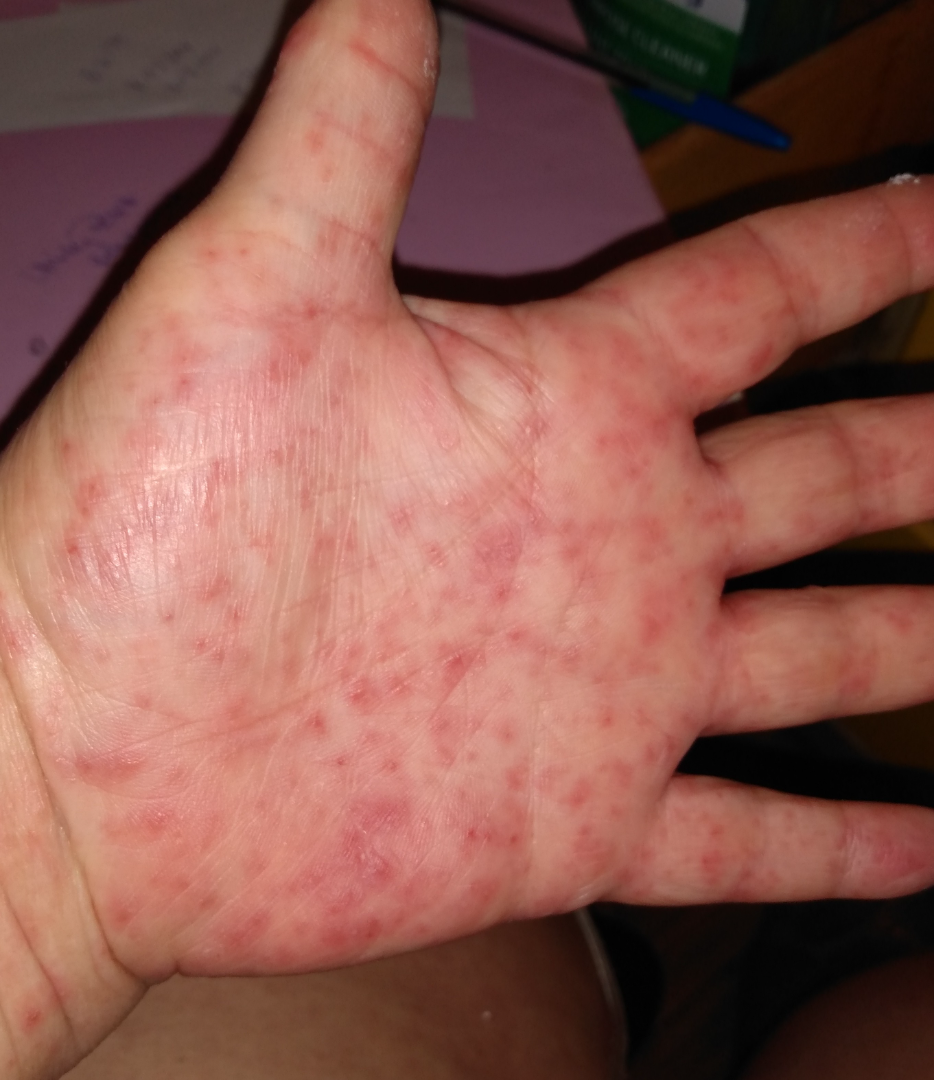Impression:
The case was difficult to assess from the available photograph.